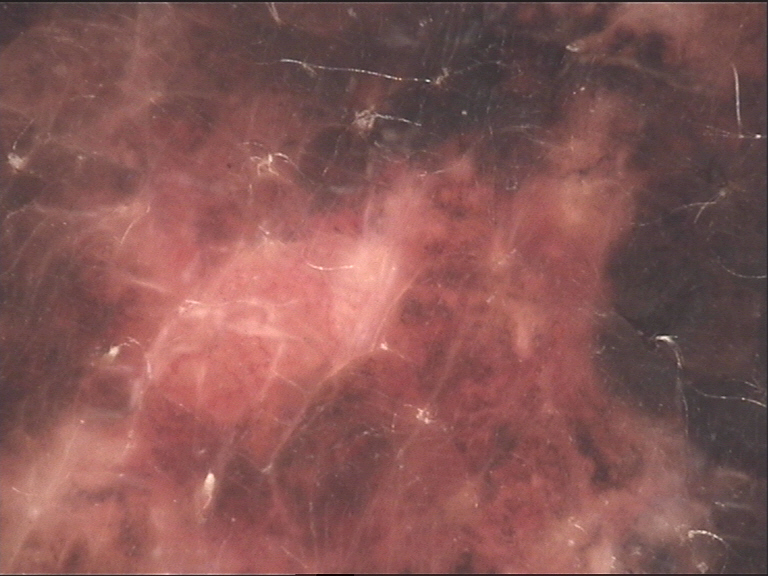• image — dermatoscopy
• diagnostic label — melanoma (biopsy-proven)